A dermoscopic photograph of a skin lesion.
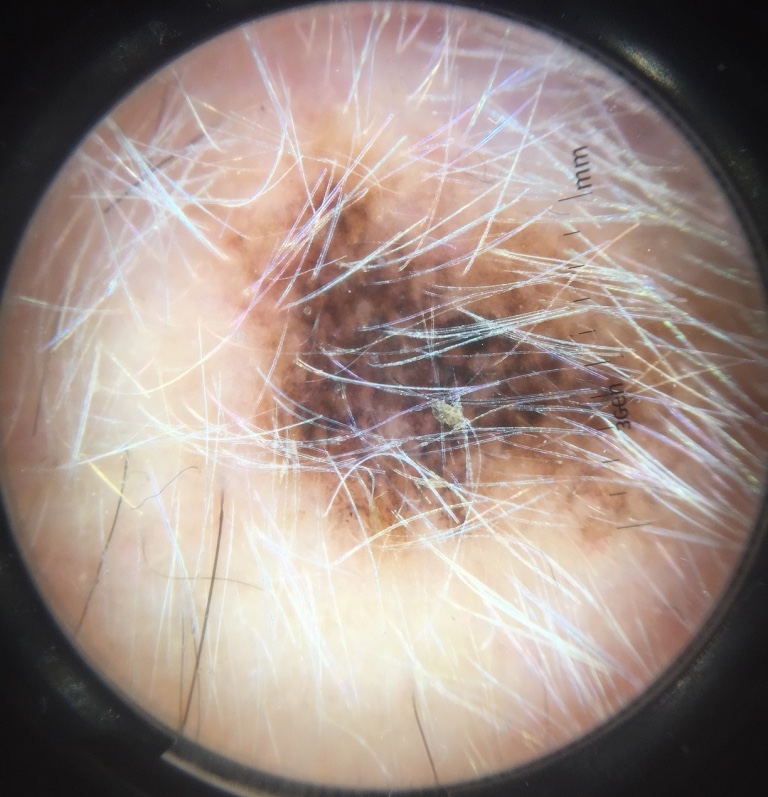label: melanoma (biopsy-proven).